A dermatoscopic image of a skin lesion.
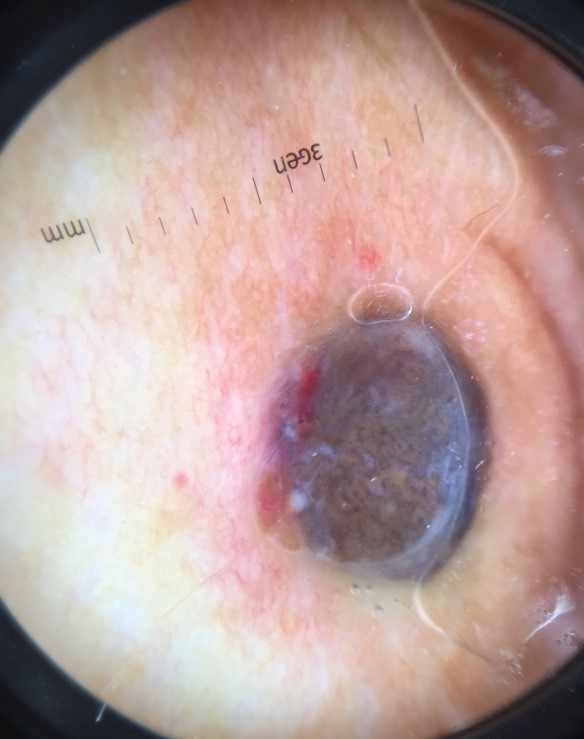Histopathology confirmed a melanoma.